A female subject, roughly 70 years of age; dermoscopy of a skin lesion.
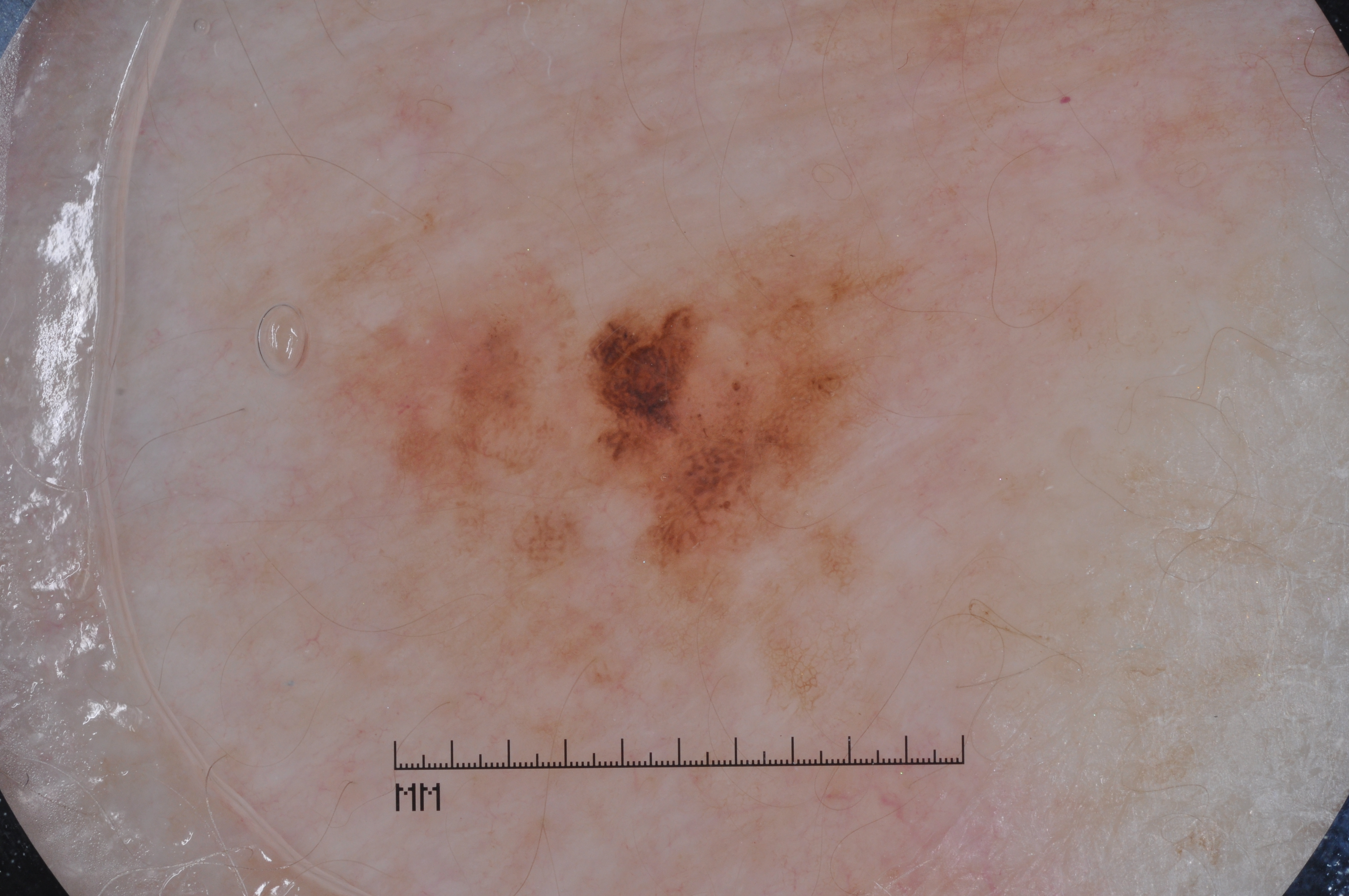A moderately sized lesion.
On dermoscopy, the lesion shows pigment network and milia-like cysts; no negative network or streaks.
The visible lesion spans bbox=[316, 231, 906, 595].
Confirmed on histopathology as a melanoma, a malignant skin lesion.